A dermoscopic close-up of a skin lesion: 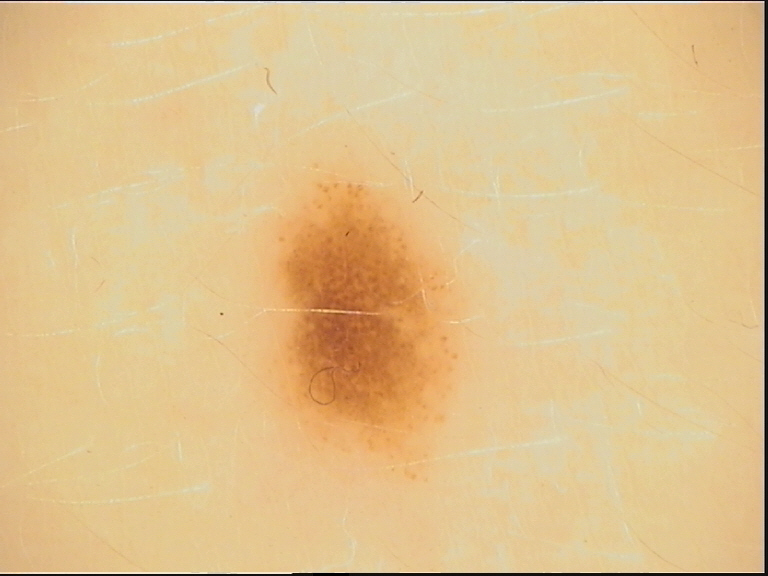diagnostic label = dysplastic junctional nevus (expert consensus).